A patient aged 52. A smartphone photograph of a skin lesion: 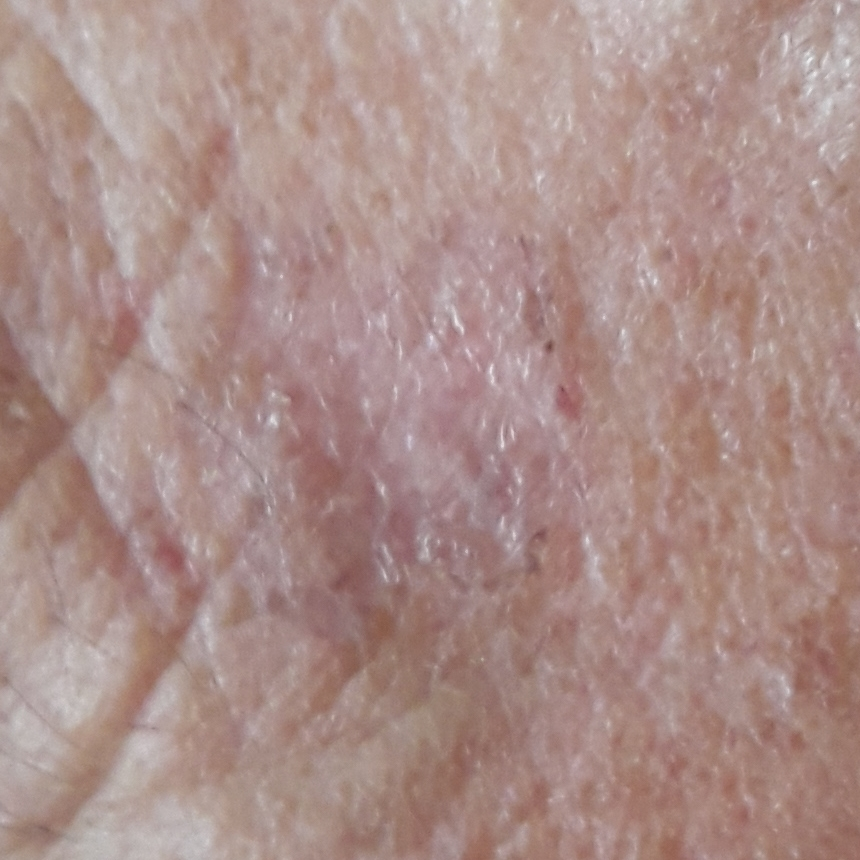Located on the face.
By the patient's account, the lesion itches.
Diagnosed by dermatologist consensus as an actinic keratosis.